This is a close-up image, texture is reported as raised or bumpy, the condition has been present for one to three months, the arm is involved, the contributor is a male aged 40–49.
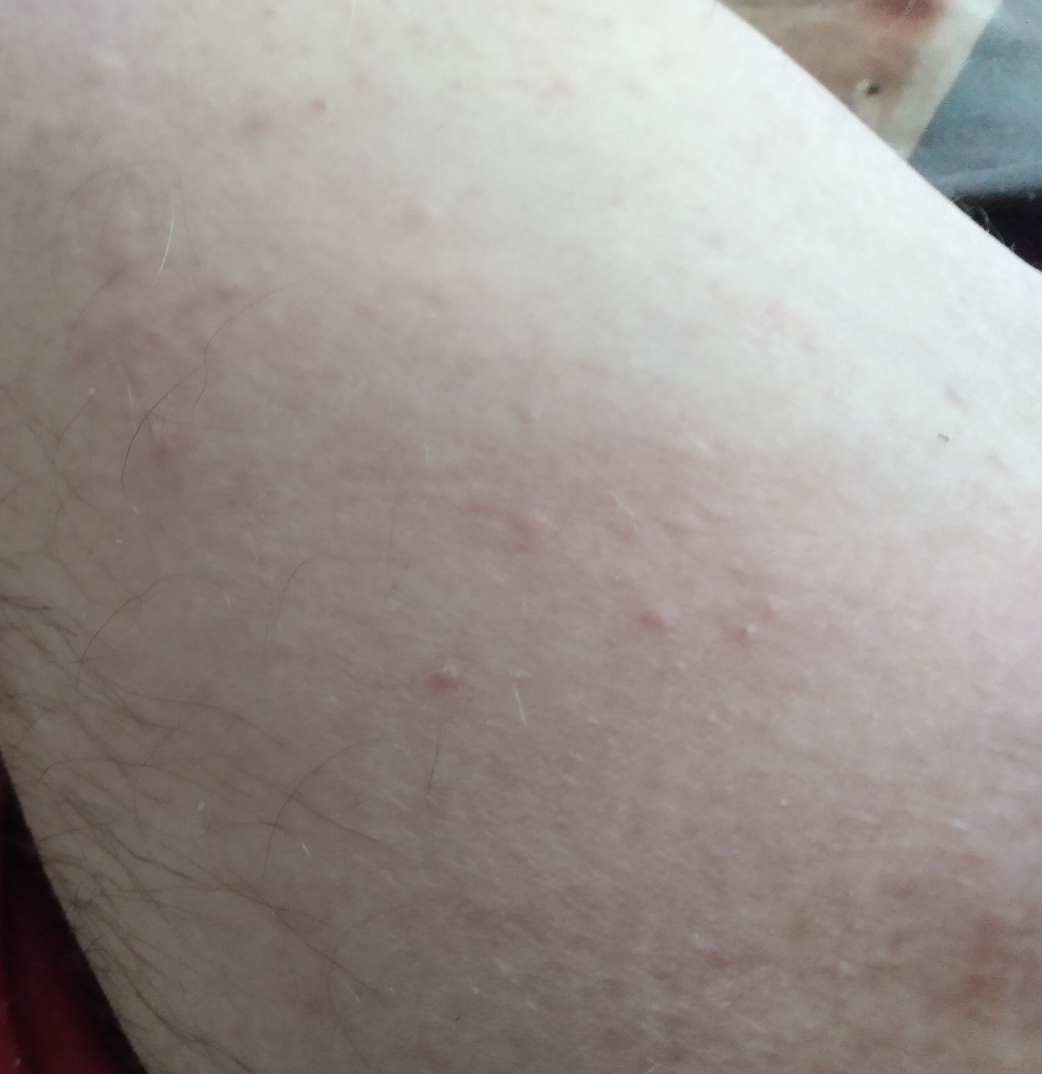<summary>
<assessment>unable to determine</assessment>
</summary>